A dermoscopic image of a skin lesion · a male subject roughly 70 years of age: 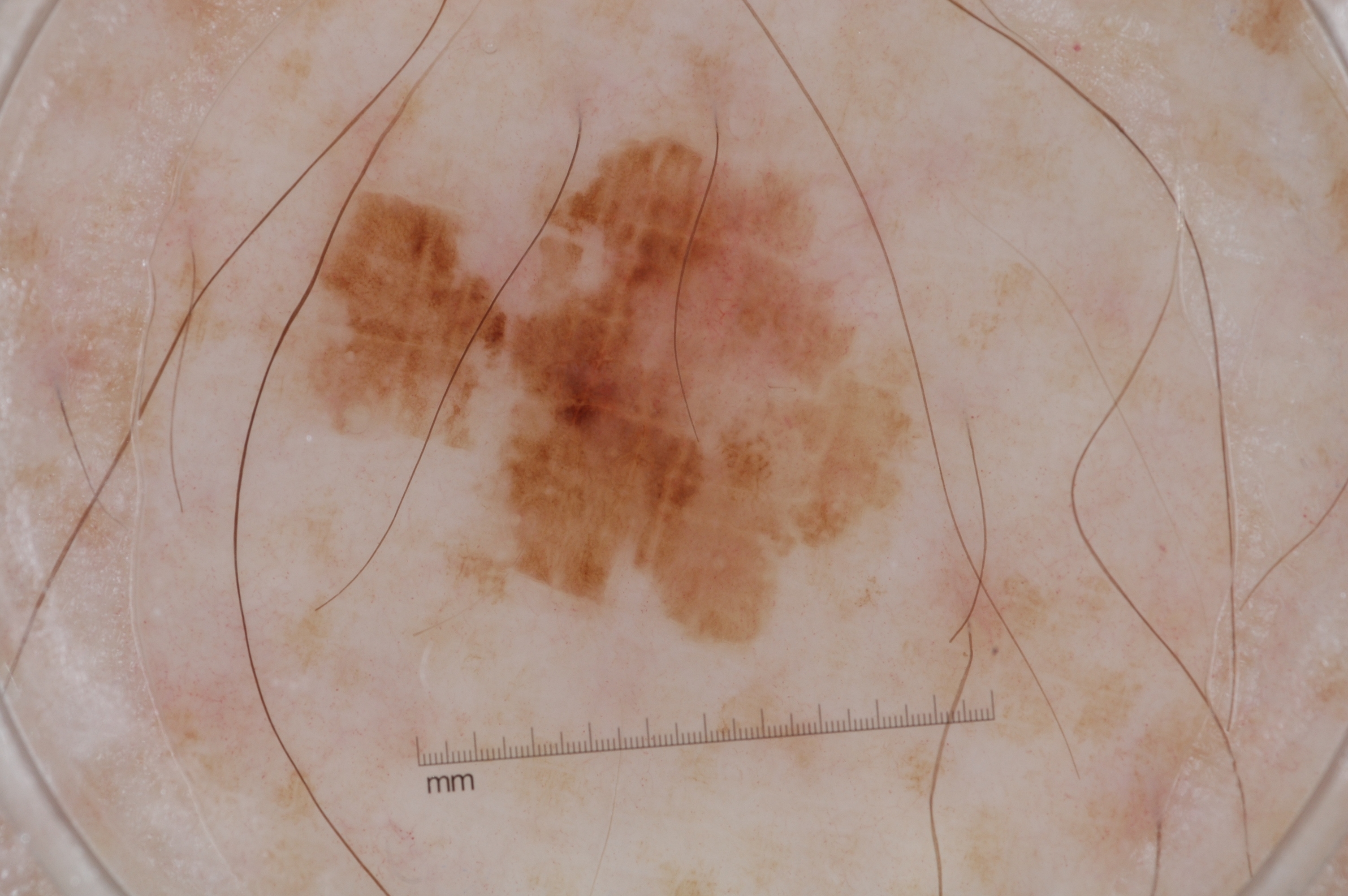lesion bbox: [317, 133, 916, 637]
absent dermoscopic findings: pigment network, negative network, milia-like cysts, and streaks
size: ~15% of the field
assessment: a seborrheic keratosis, a lesion of keratinocytic origin